A skin lesion imaged with a dermatoscope.
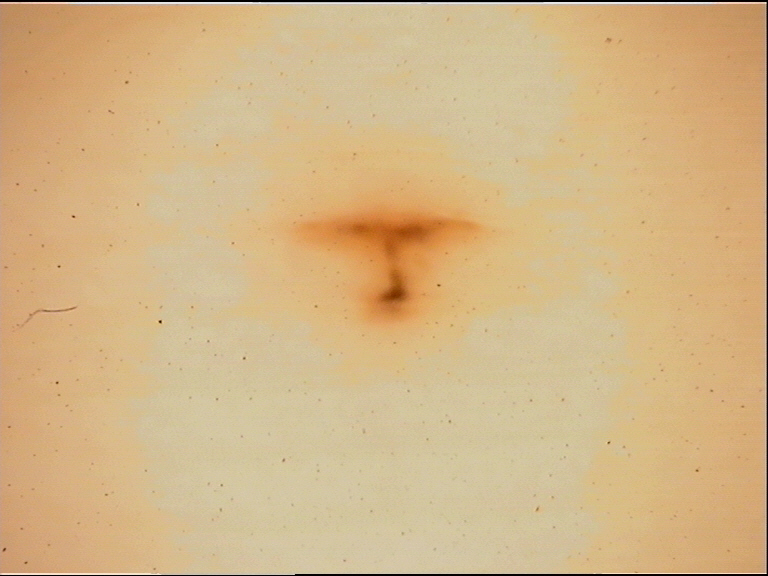| field | value |
|---|---|
| class | acral junctional nevus (expert consensus) |